The photograph was taken at an angle · the subject is a male aged 18–29.
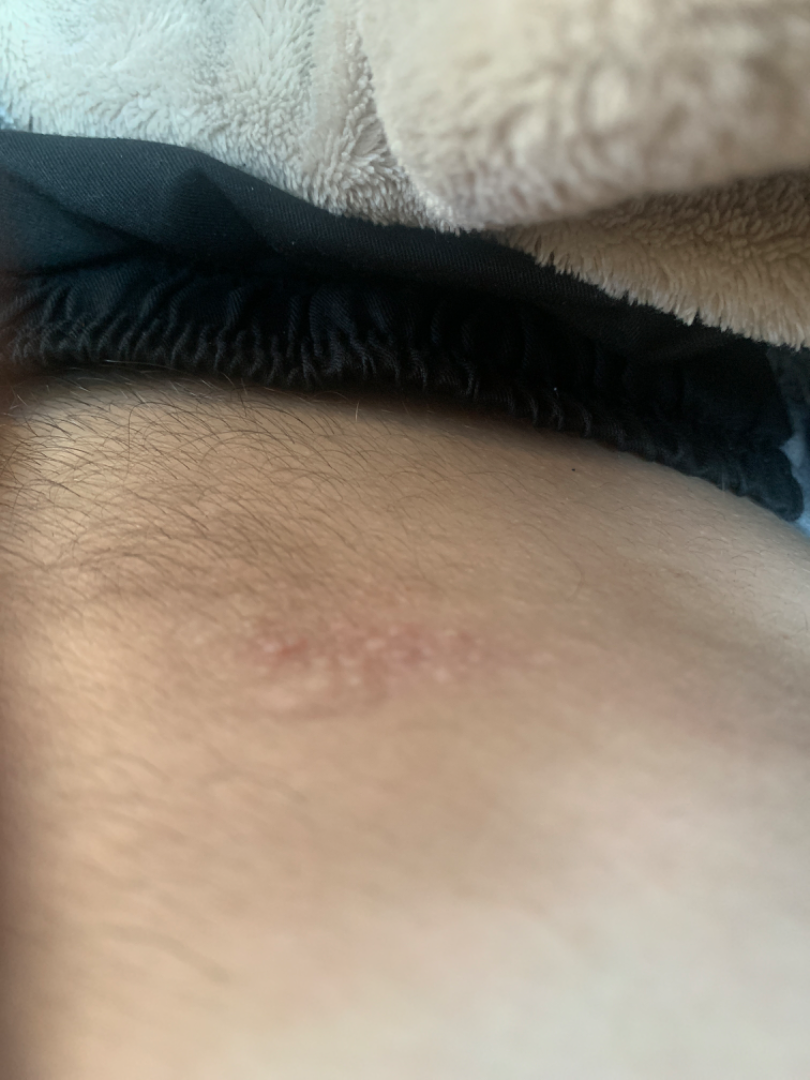No differential diagnosis could be assigned on photographic review. The patient described the issue as a rash. FST III. The patient notes the lesion is raised or bumpy.